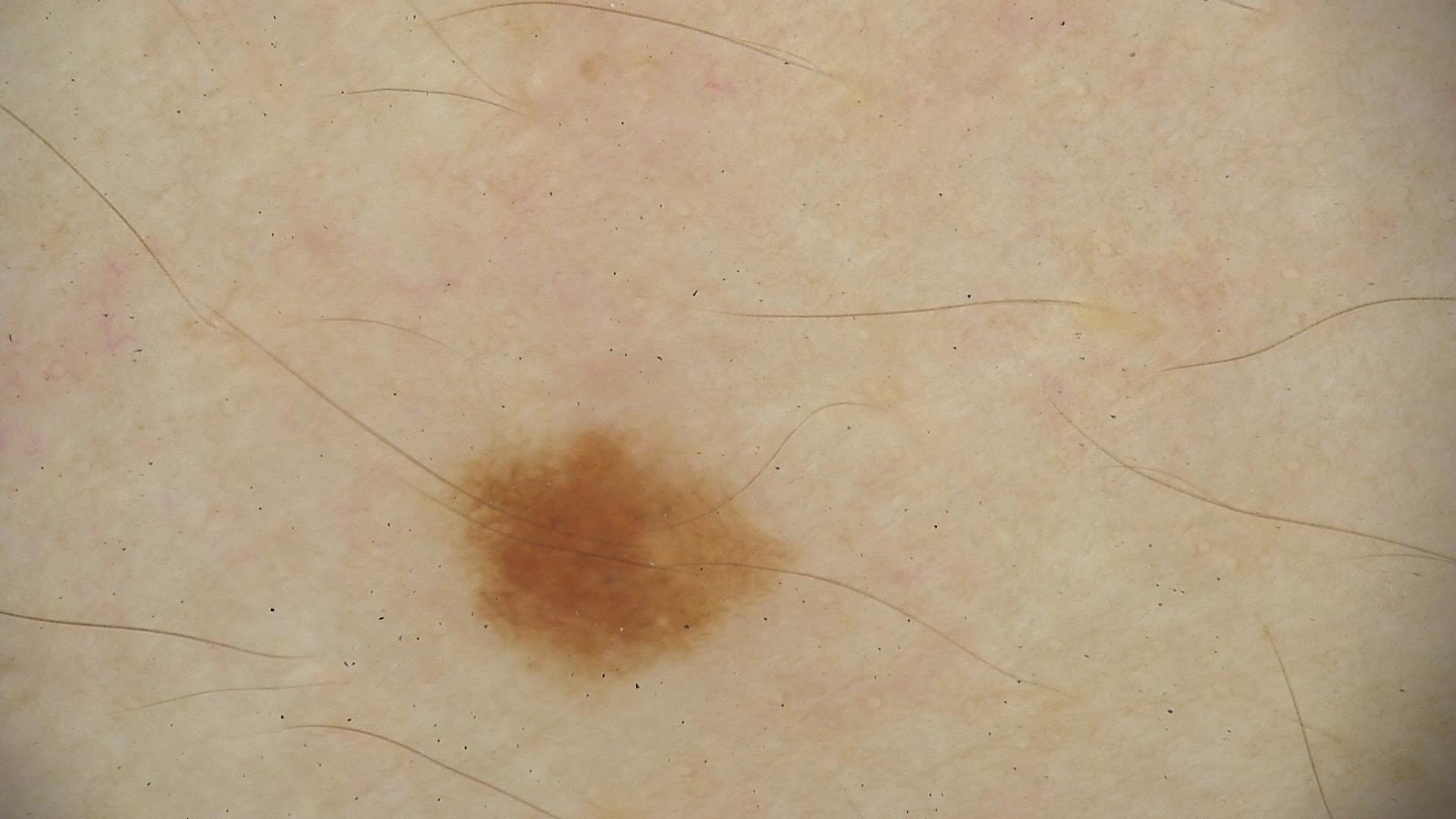<case>
<diagnosis>
<name>junctional nevus</name>
<code>jb</code>
<malignancy>benign</malignancy>
<super_class>melanocytic</super_class>
<confirmation>expert consensus</confirmation>
</diagnosis>
</case>